The affected area is the leg; the photograph was taken at a distance; the contributor is 60–69, female:
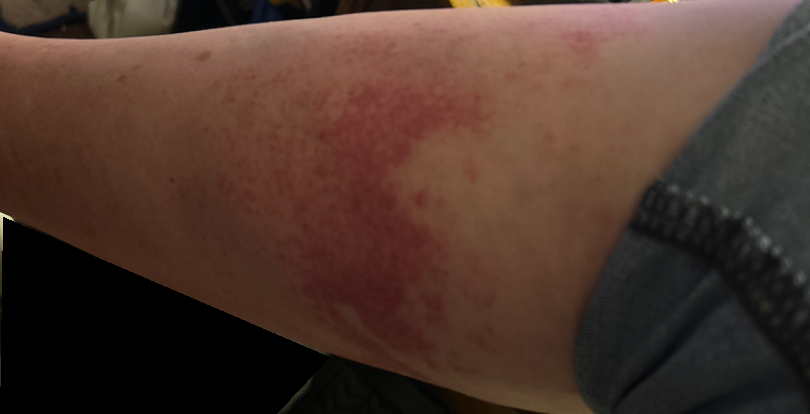diagnostic considerations = in keeping with Leukocytoclastic Vasculitis